The lesion involves the leg and arm; the subject is a female aged 40–49; an image taken at a distance — 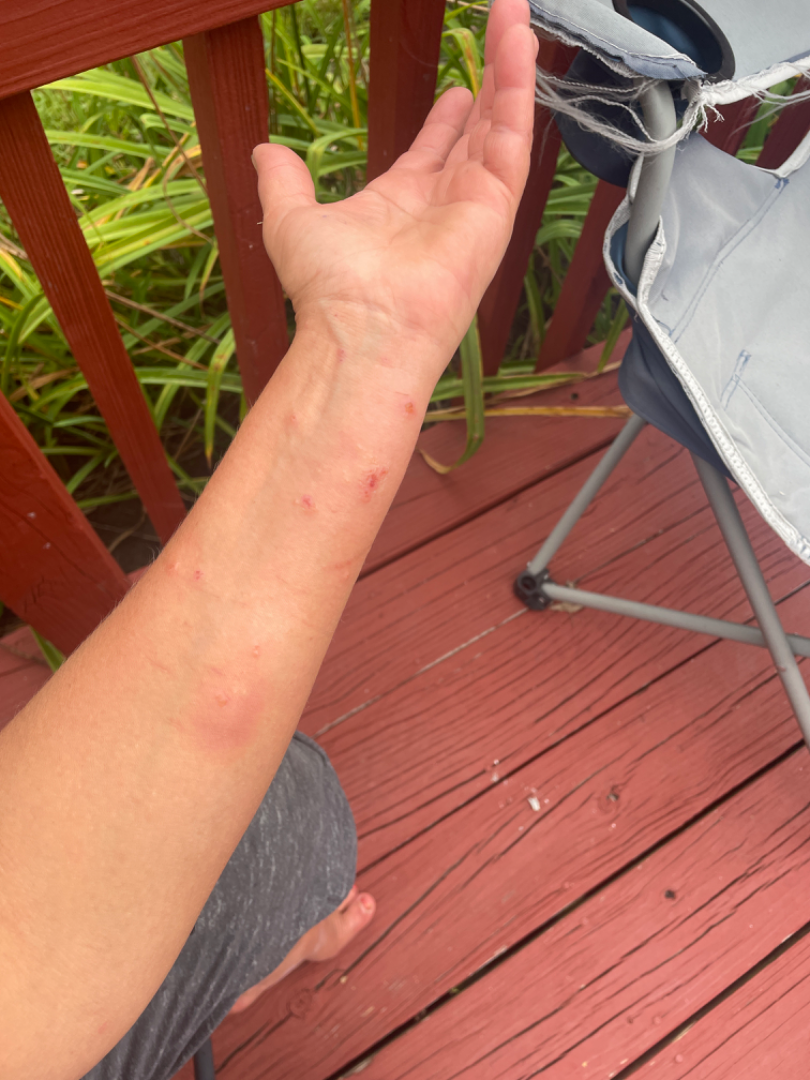Case summary:
– assessment — the leading impression is Allergic Contact Dermatitis; the differential also includes Contact dermatitis; less probable is Herpes Zoster